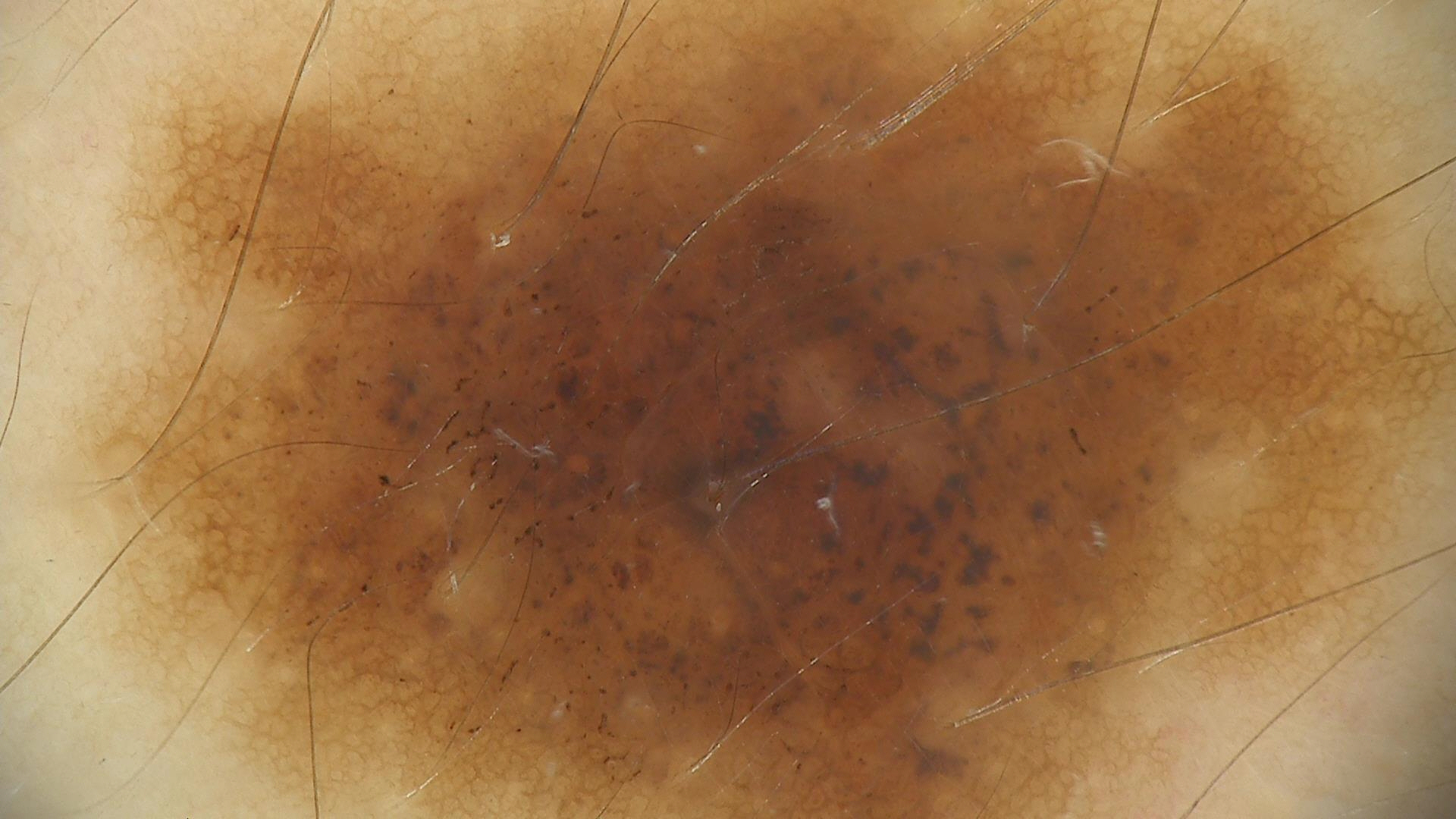Impression:
Classified as a dysplastic compound nevus.